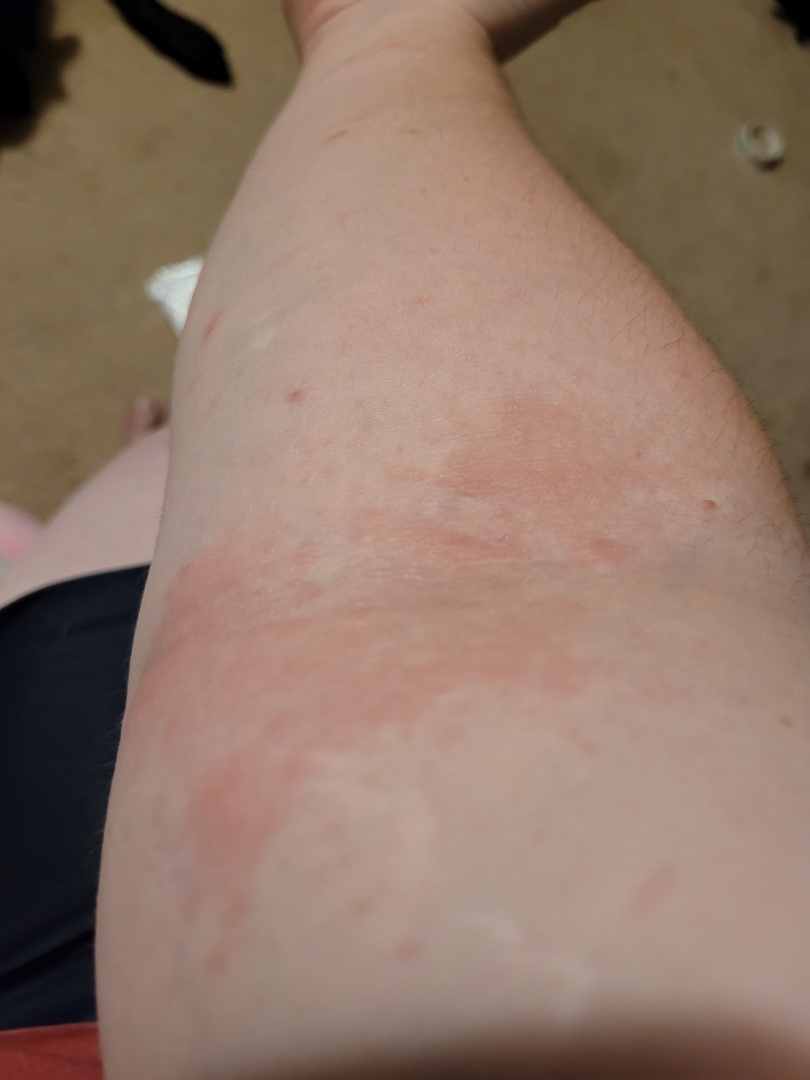symptom duration = less than one week
location = arm
systemic symptoms = none reported
patient-reported symptoms = itching, bothersome appearance and enlargement
self-categorized as = a rash
shot type = at an angle
contributor = female, age 30–39
differential = reviewed remotely by one dermatologist: the reviewer's impression was Eczema